A skin lesion imaged with a dermatoscope: 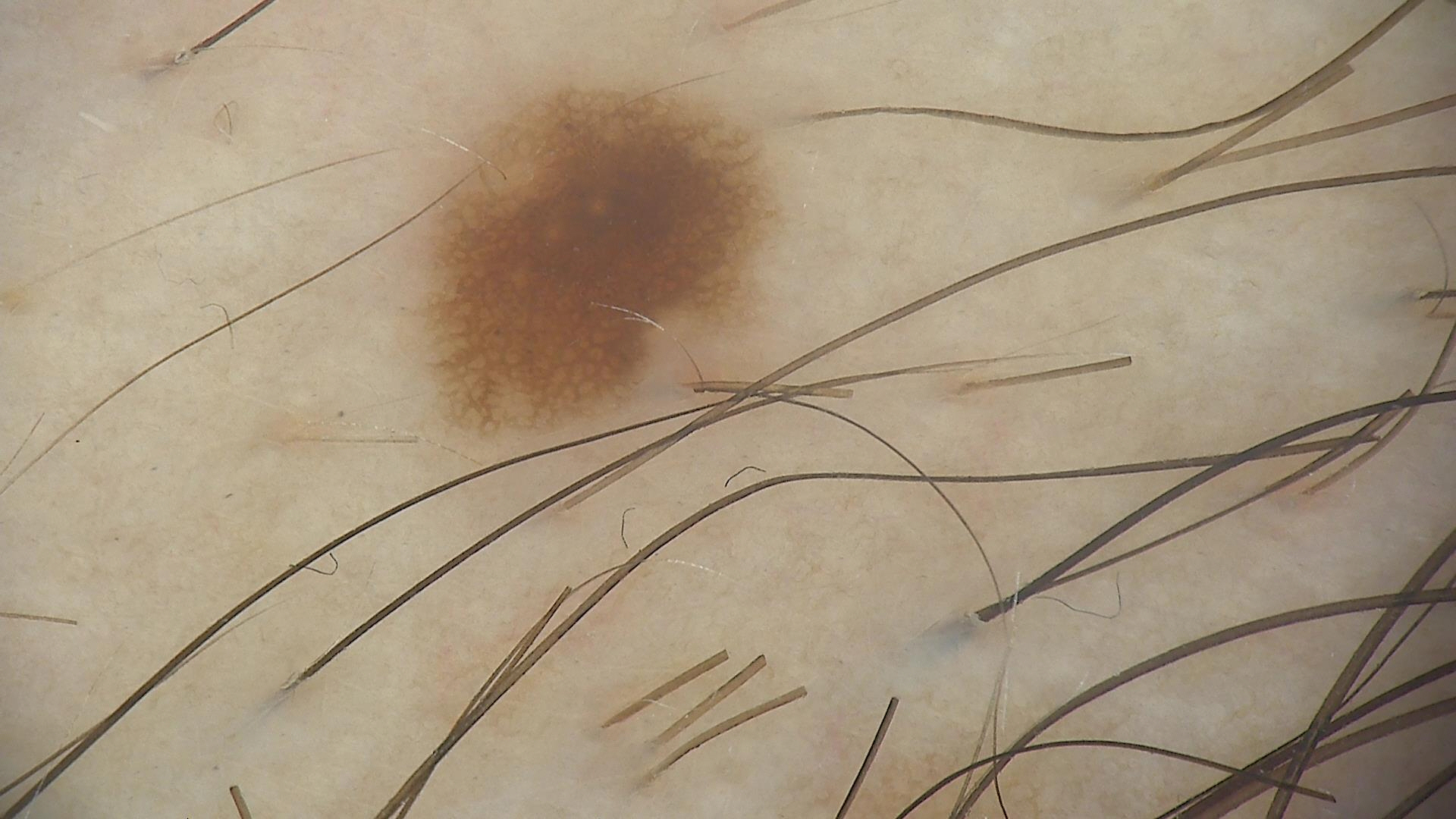Labeled as a dysplastic junctional nevus.